A dermatoscopic image of a skin lesion.
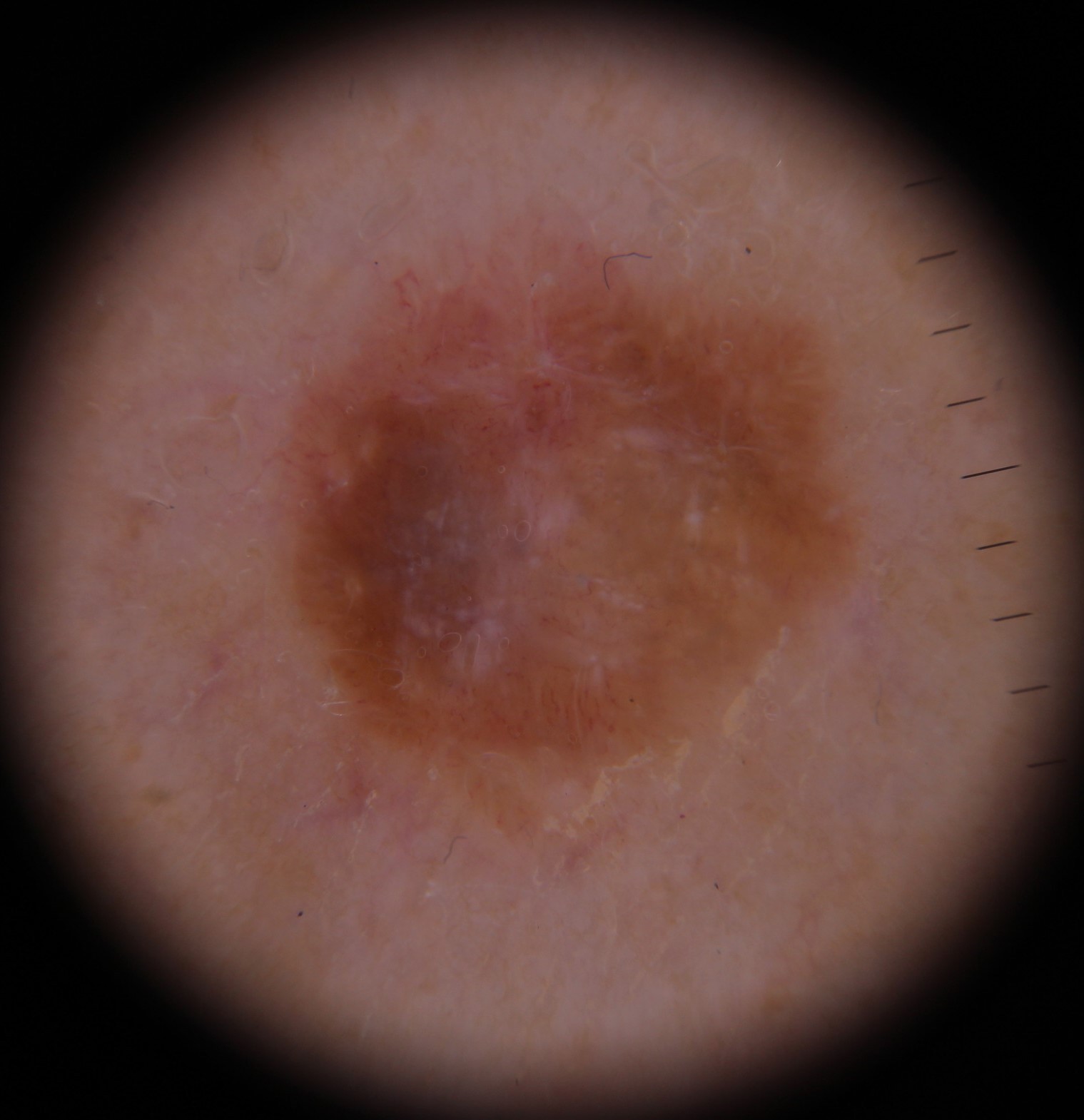class = melanoma (biopsy-proven).